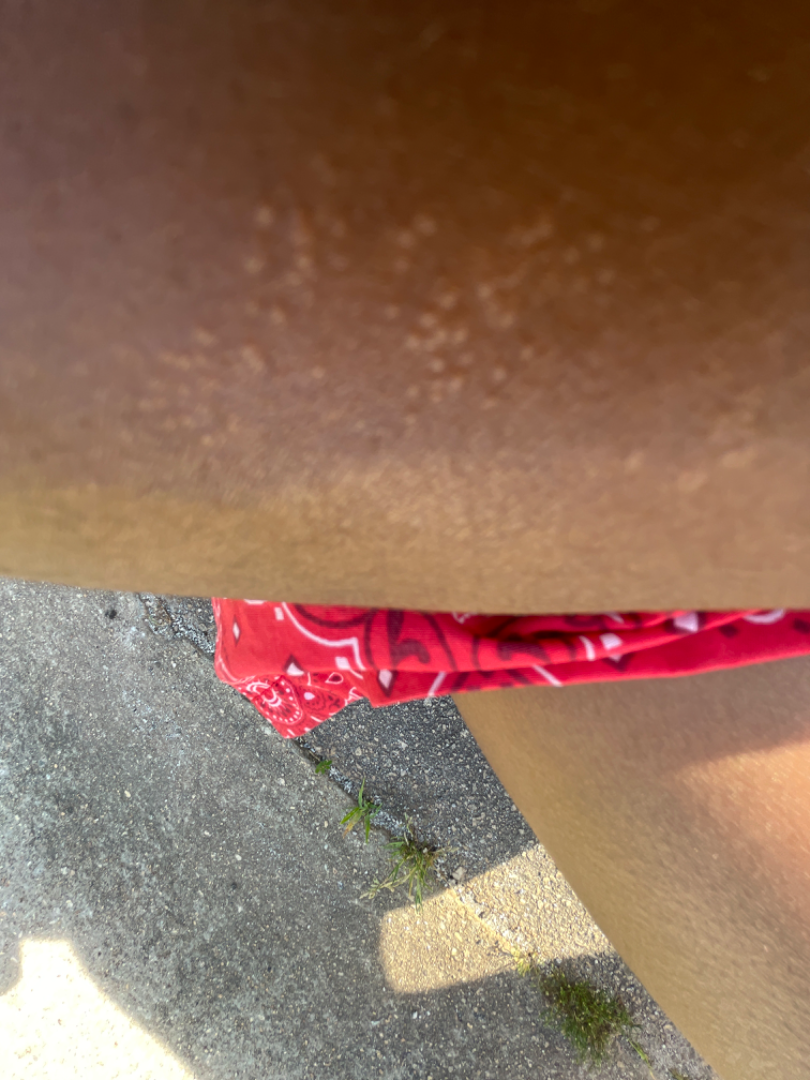The skin findings could not be characterized from the image. FST V. The affected area is the arm. The patient described the issue as a rash. A close-up photograph. The patient reports the condition has been present for one to four weeks. Male subject, age 18–29. The patient reports the lesion is raised or bumpy.